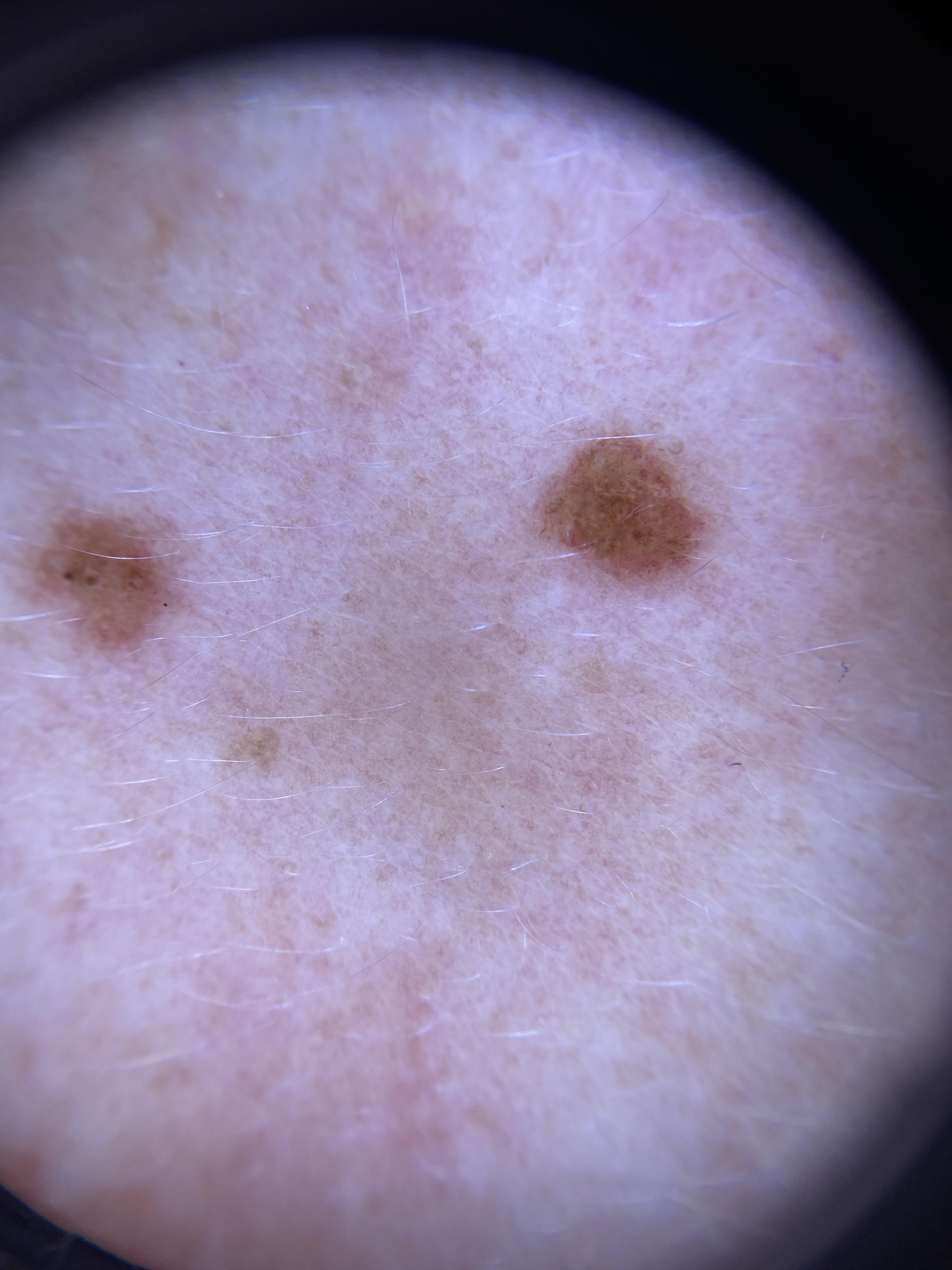Q: Who is the patient?
A: female, aged around 35
Q: What was the clinical impression?
A: Nevus